A dermoscopic image of a skin lesion: 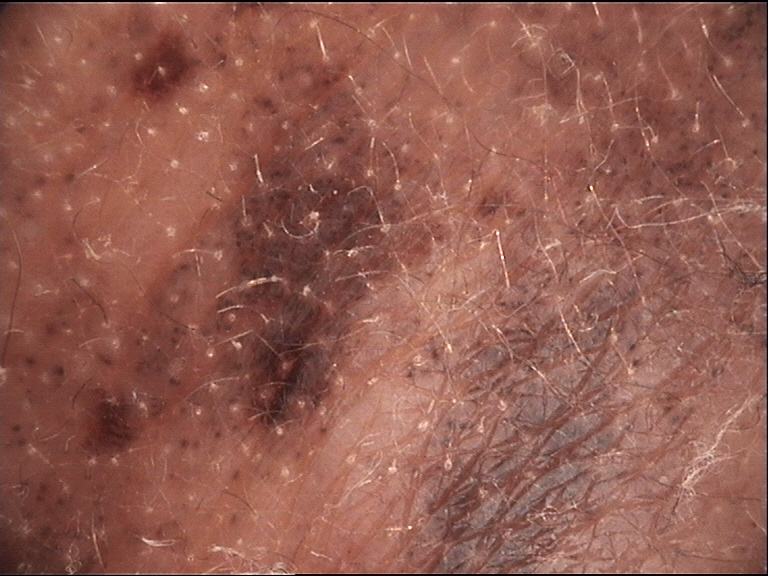Q: What is the lesion category?
A: banal
Q: What is this lesion?
A: congenital compound nevus (expert consensus)